A dermoscopic photograph of a skin lesion: 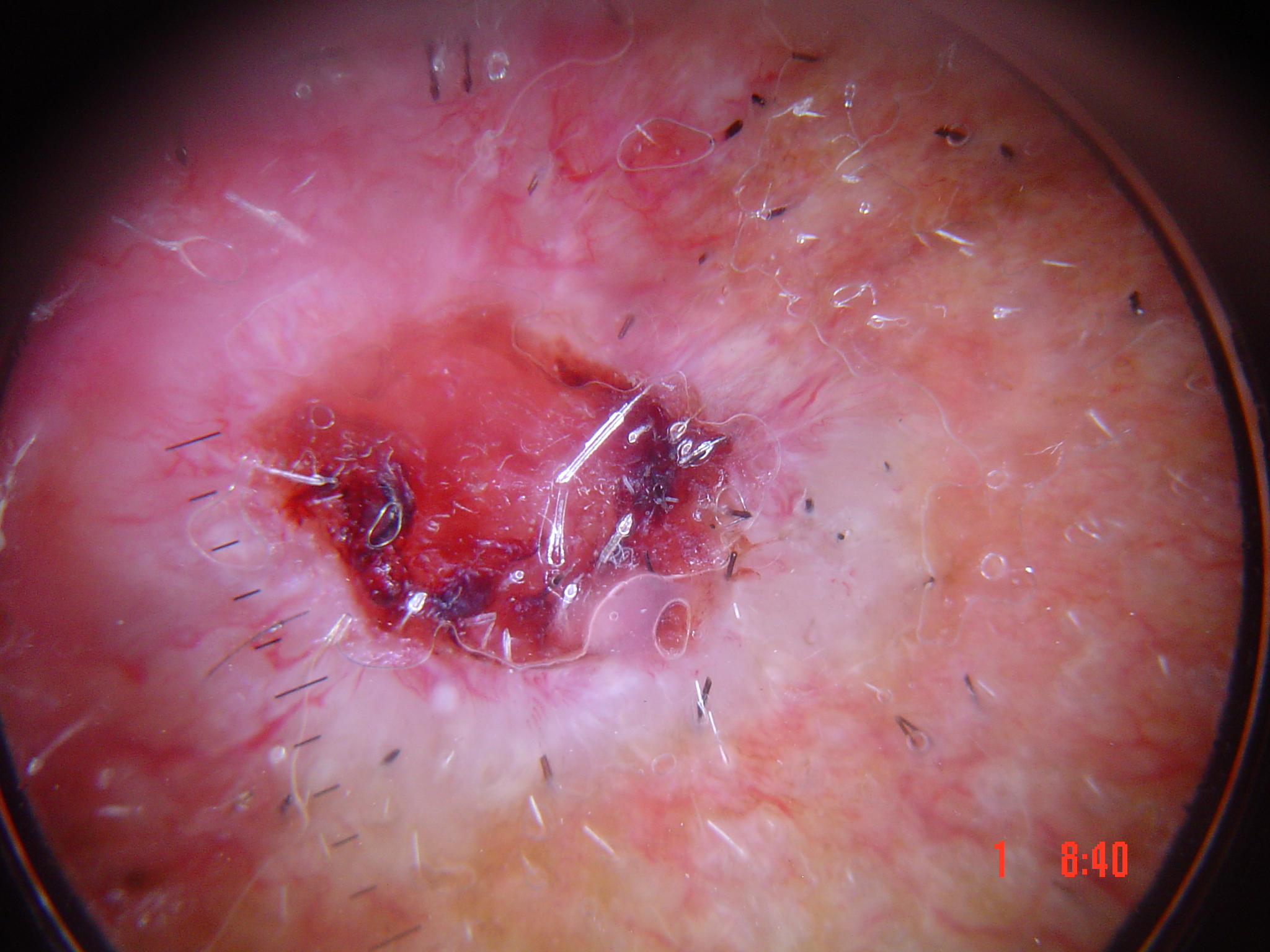classification — keratinocytic | class — basal cell carcinoma (biopsy-proven).